A female subject, in their mid-50s; this is a dermoscopic photograph of a skin lesion — 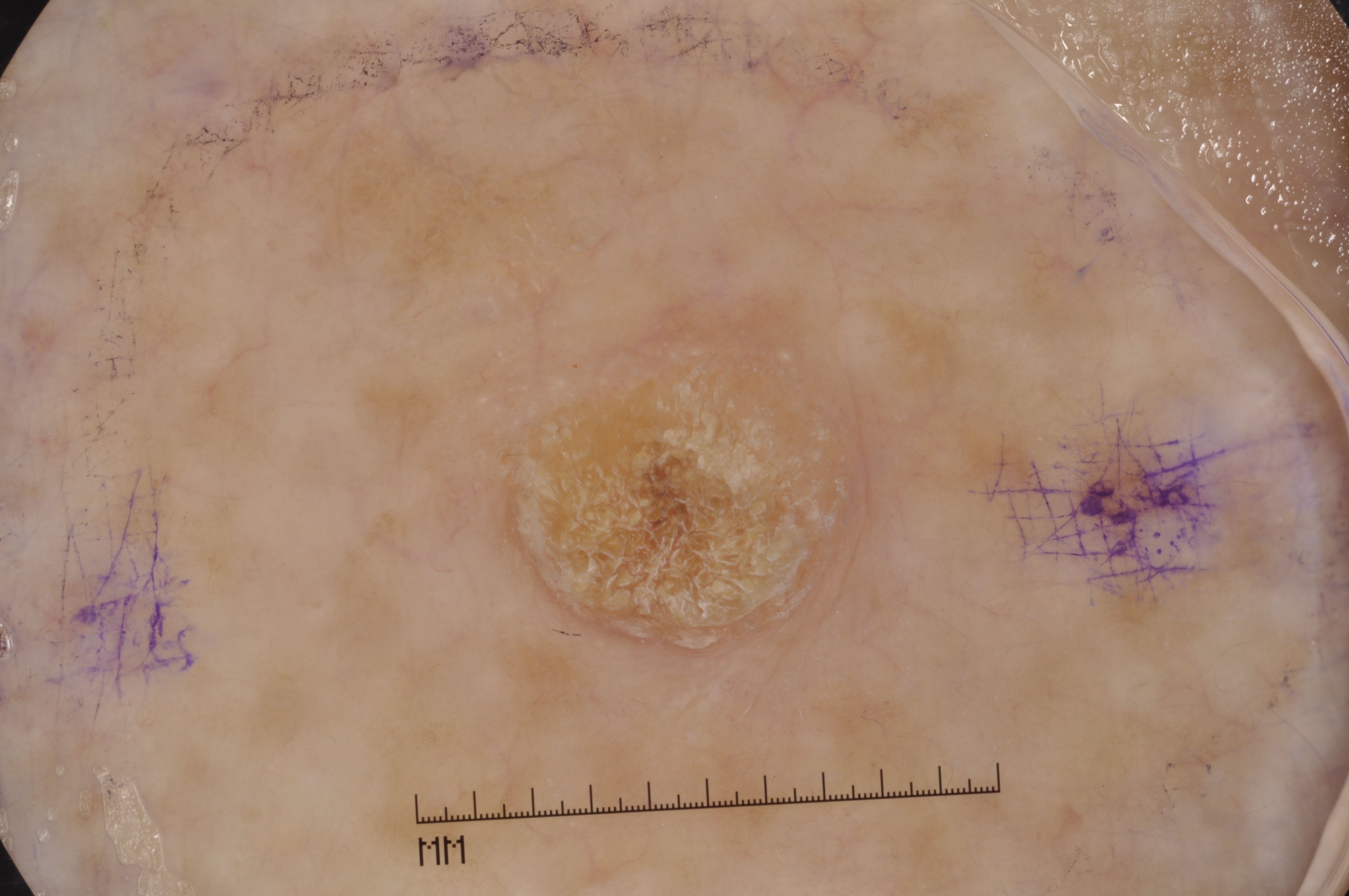Q: Which dermoscopic features are absent?
A: negative network, pigment network, streaks, and milia-like cysts
Q: How much of the field does the lesion occupy?
A: moderate
Q: What is the lesion's bounding box?
A: box(509, 320, 878, 667)
Q: What is this lesion?
A: a seborrheic keratosis, a benign lesion